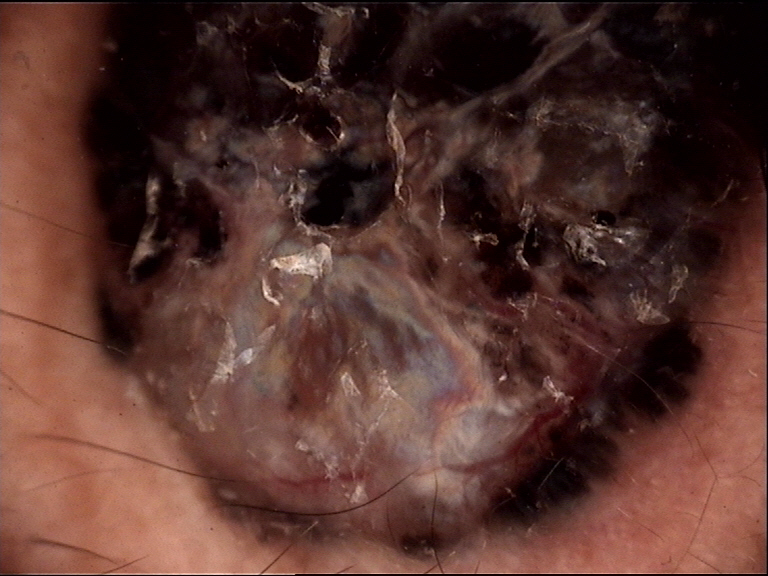Case:
– class: melanoma (biopsy-proven)